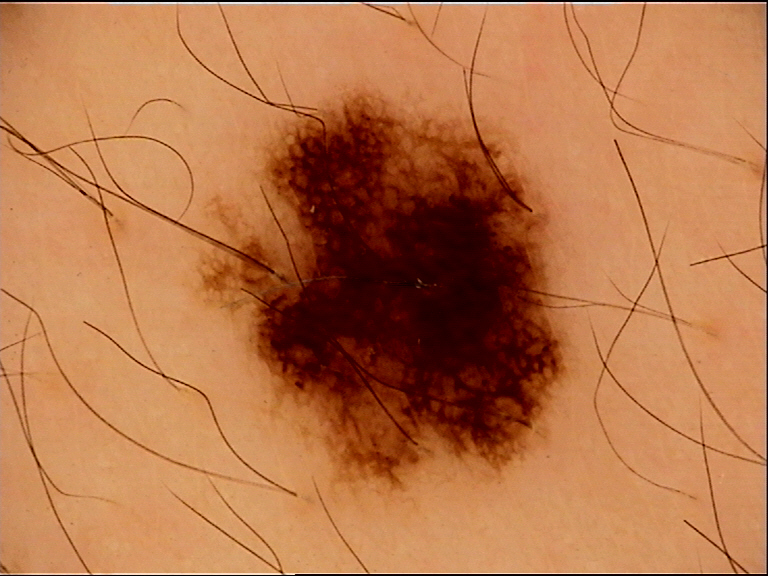* assessment: dysplastic junctional nevus (expert consensus)